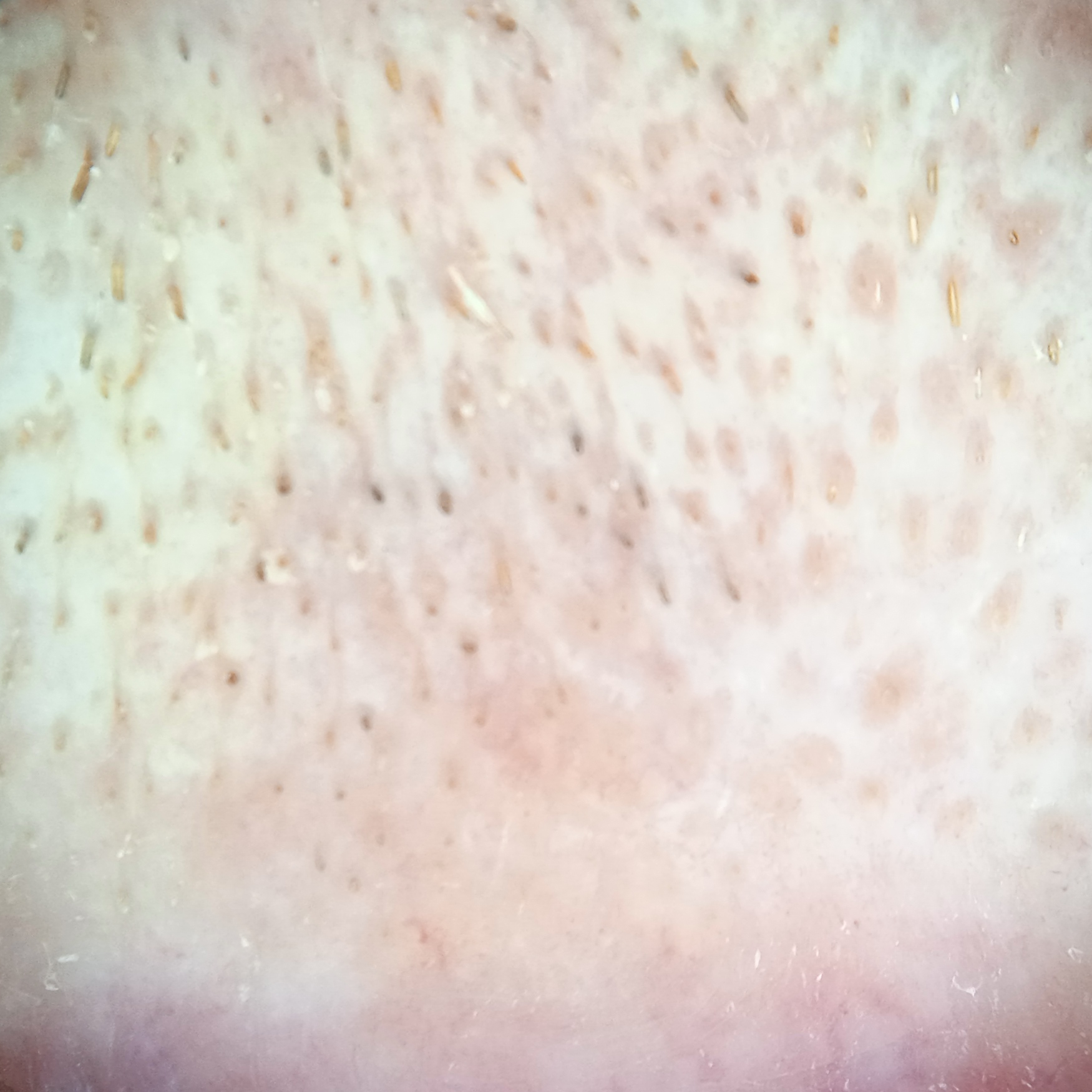{"sun_reaction": "skin reddens with sun exposure", "patient": {"age": 77, "sex": "male"}, "risk_factors": {"positive": ["a personal history of skin cancer", "a personal history of cancer"], "negative": ["no prior organ transplant", "no sunbed use"]}, "mole_burden": "a moderate number of melanocytic nevi", "image": "dermatoscopic image", "lesion_location": "the face", "lesion_size": {"diameter_mm": 6.4}, "diagnosis": {"name": "actinic keratosis", "malignancy": "benign"}}